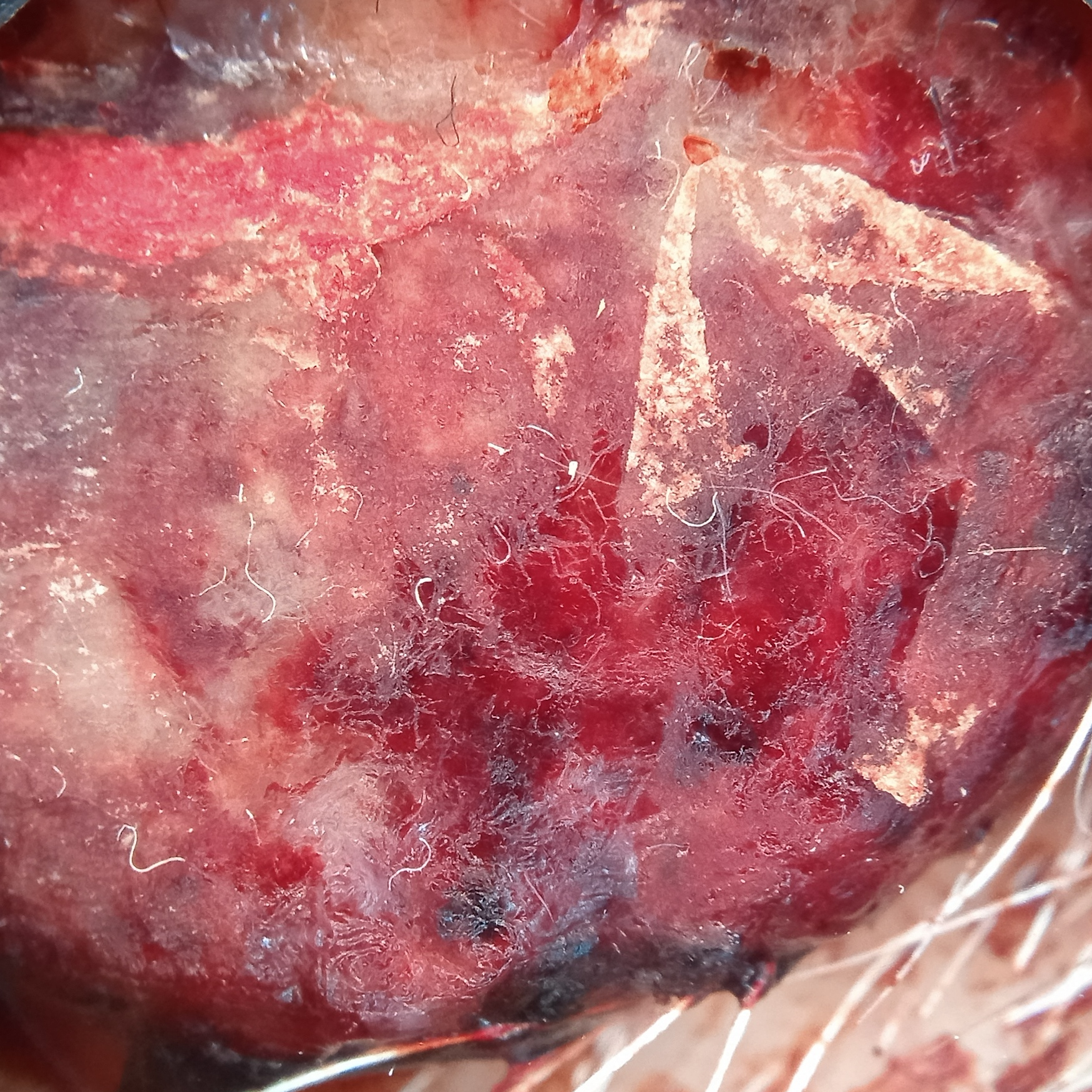Findings:
- diagnosis: melanoma (biopsy-proven)